A male patient aged 48. A clinical close-up photograph of a skin lesion:
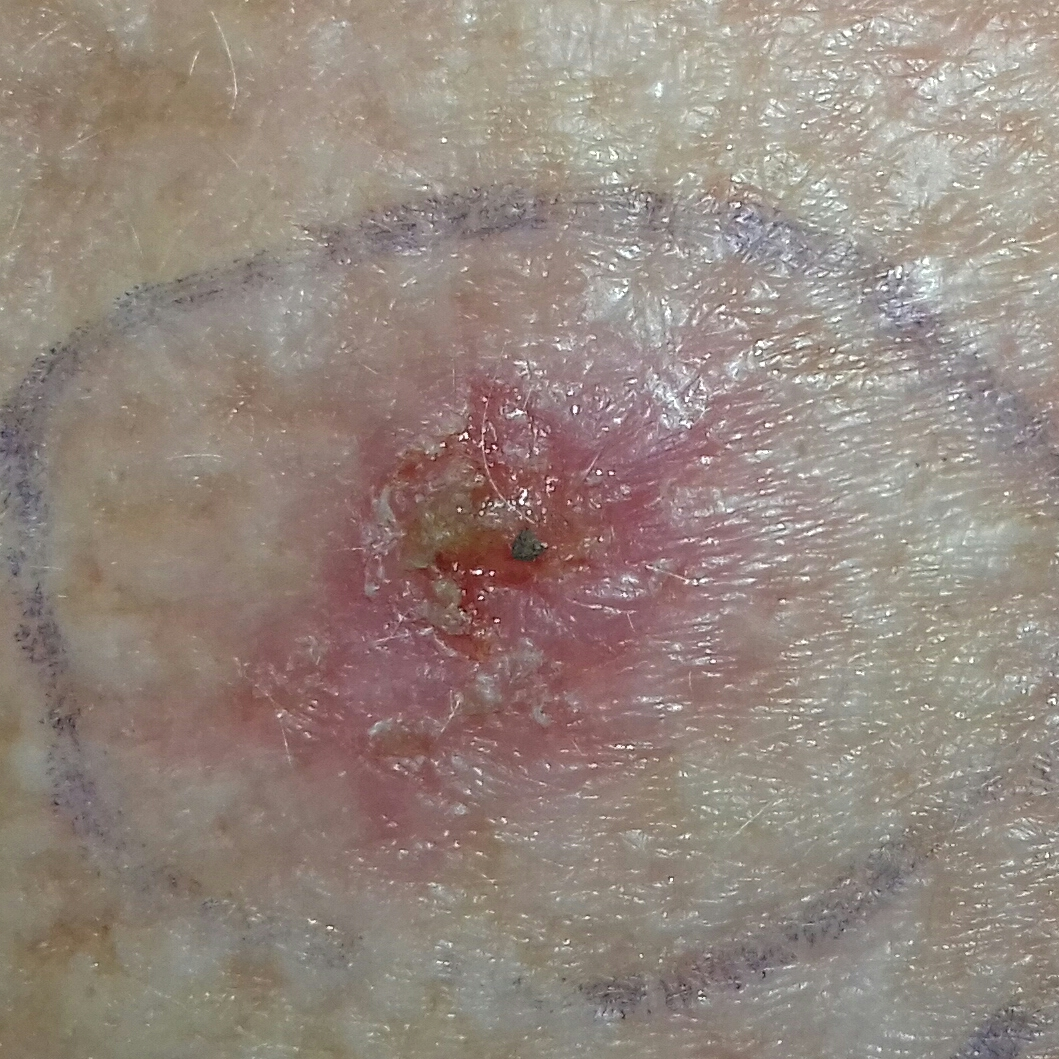• pathology: basal cell carcinoma (biopsy-proven)